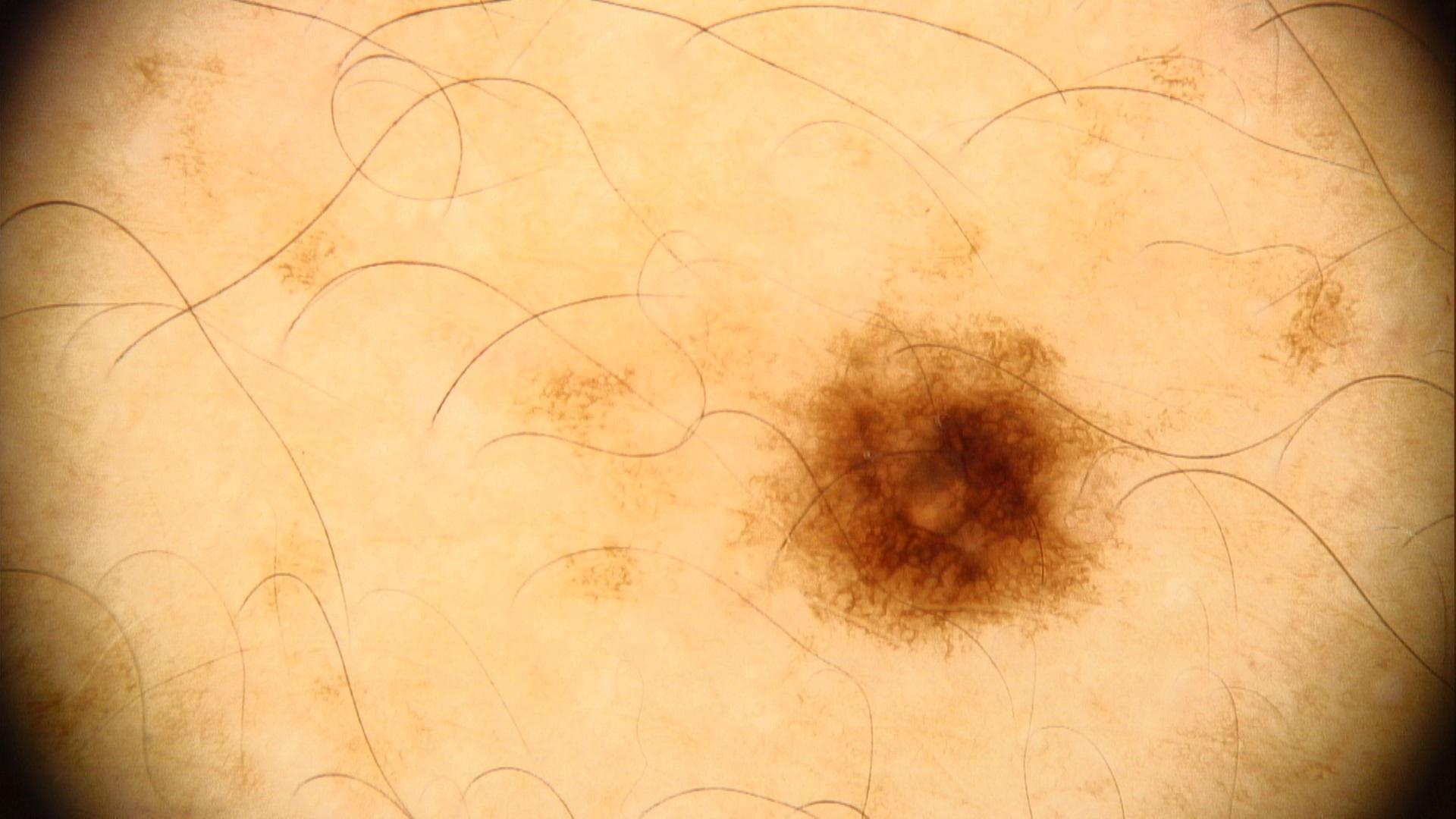Clinically diagnosed as a nevus.